The arm is involved. A close-up photograph:
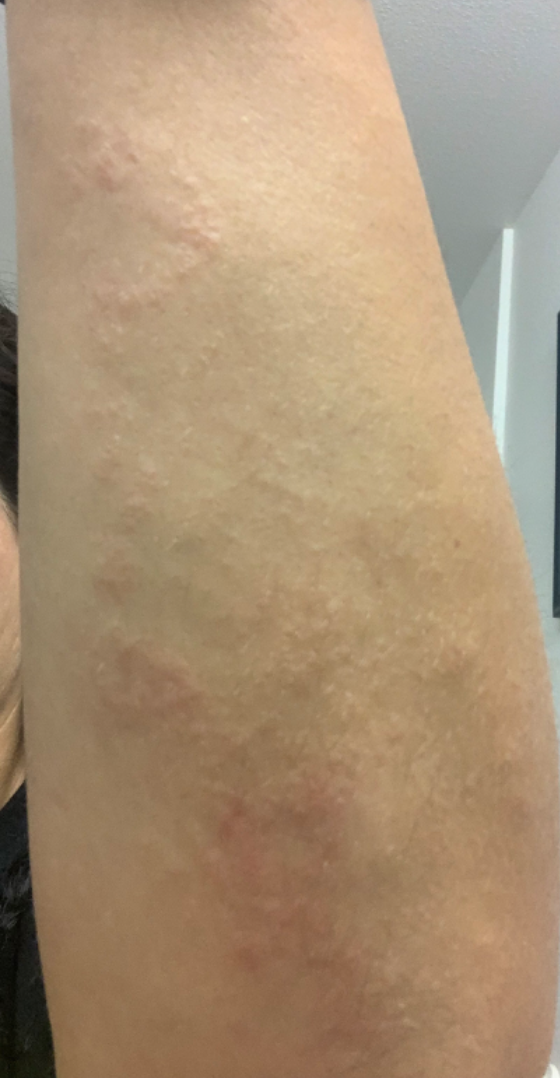Eczema (considered); Allergic Contact Dermatitis (considered); Psoriasis (lower probability).